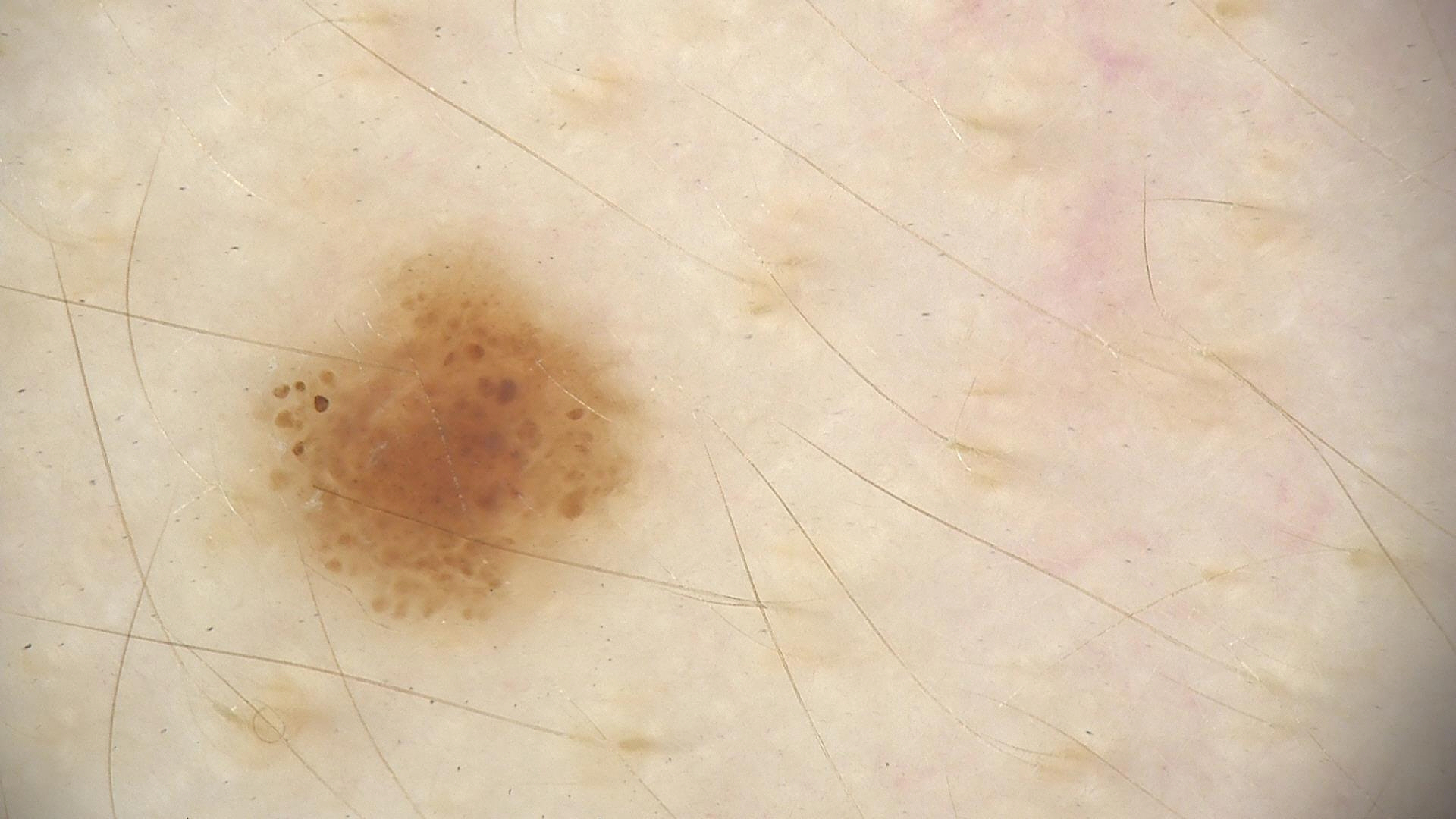label: dysplastic junctional nevus (expert consensus).